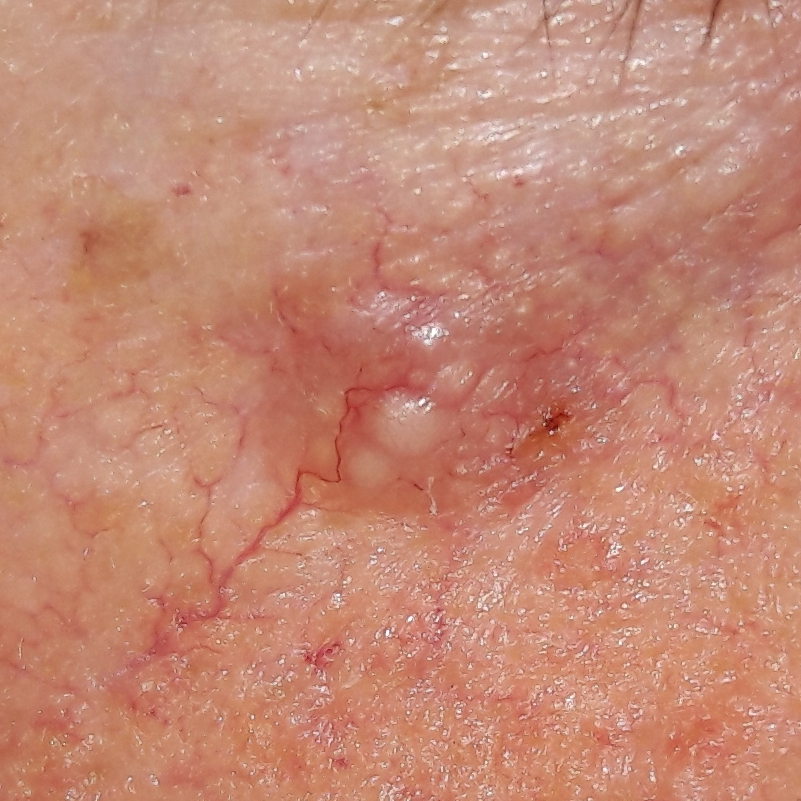image = clinical photo; exposure history = prior skin cancer (patient or family); location = the face; symptoms = elevation, itching / no growth, no bleeding; diagnostic label = basal cell carcinoma (biopsy-proven).